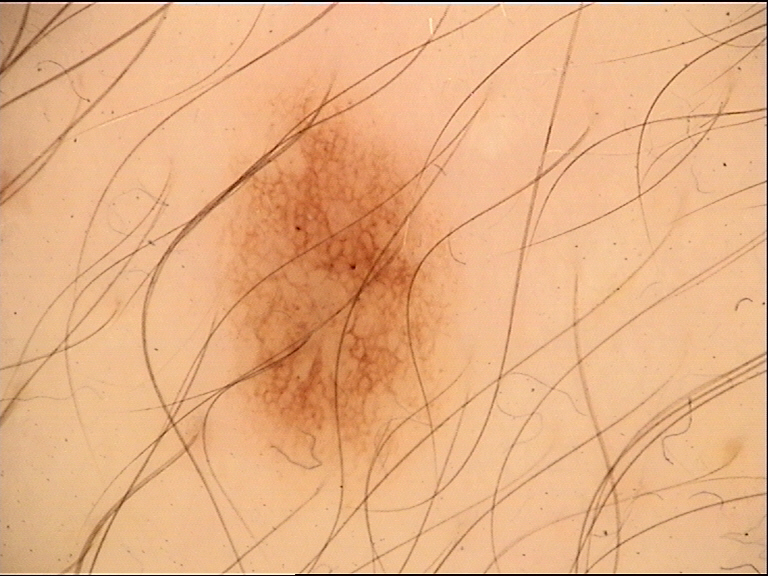A dermoscopic photograph of a skin lesion.
Diagnosed as a benign lesion — a dysplastic junctional nevus.